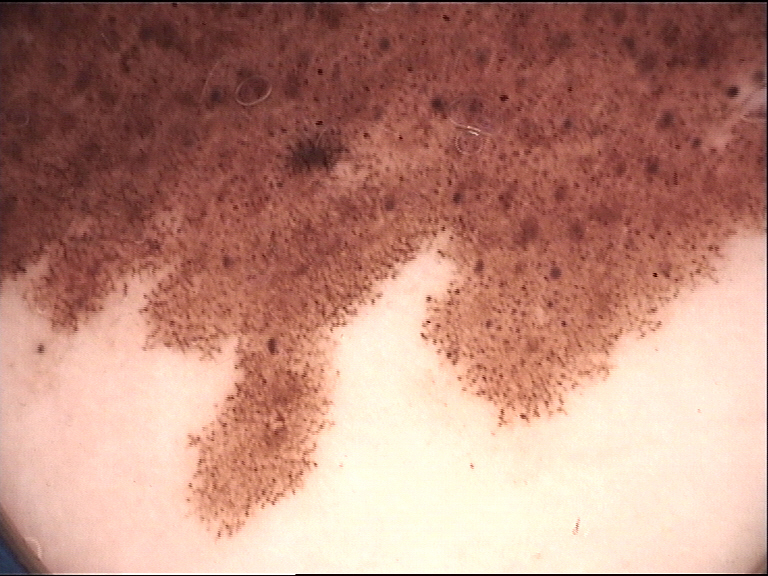category: banal; class: congenital compound nevus (expert consensus).